Recorded as Fitzpatrick phototype II. A male subject approximately 55 years of age.
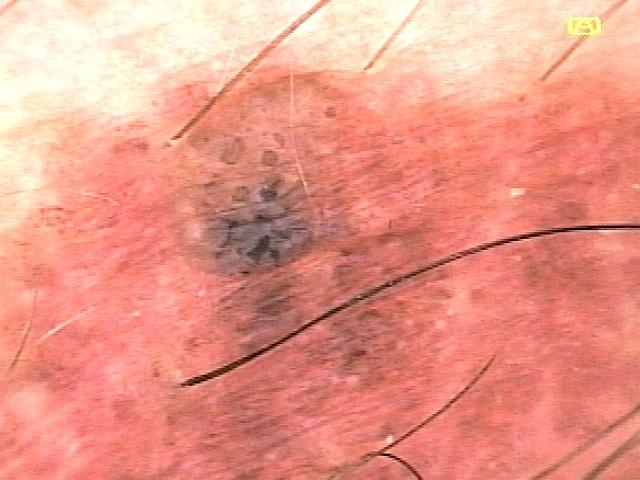Image and clinical context: The lesion is located on the trunk, specifically the posterior trunk. Diagnosis: Histopathology confirmed a benign, melanocytic lesion — a nevus.